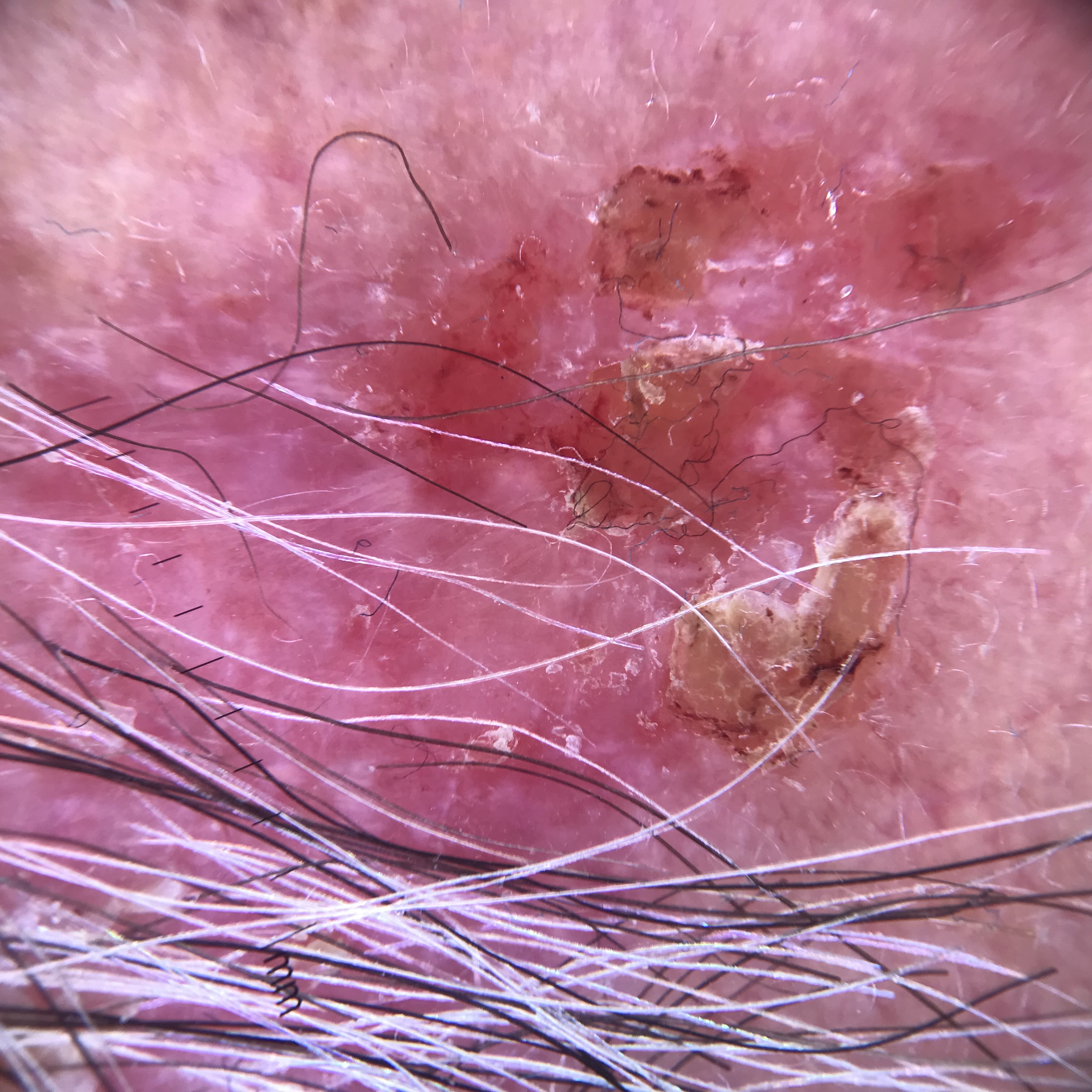image — dermatoscopy; class — Bowen's disease (biopsy-proven).